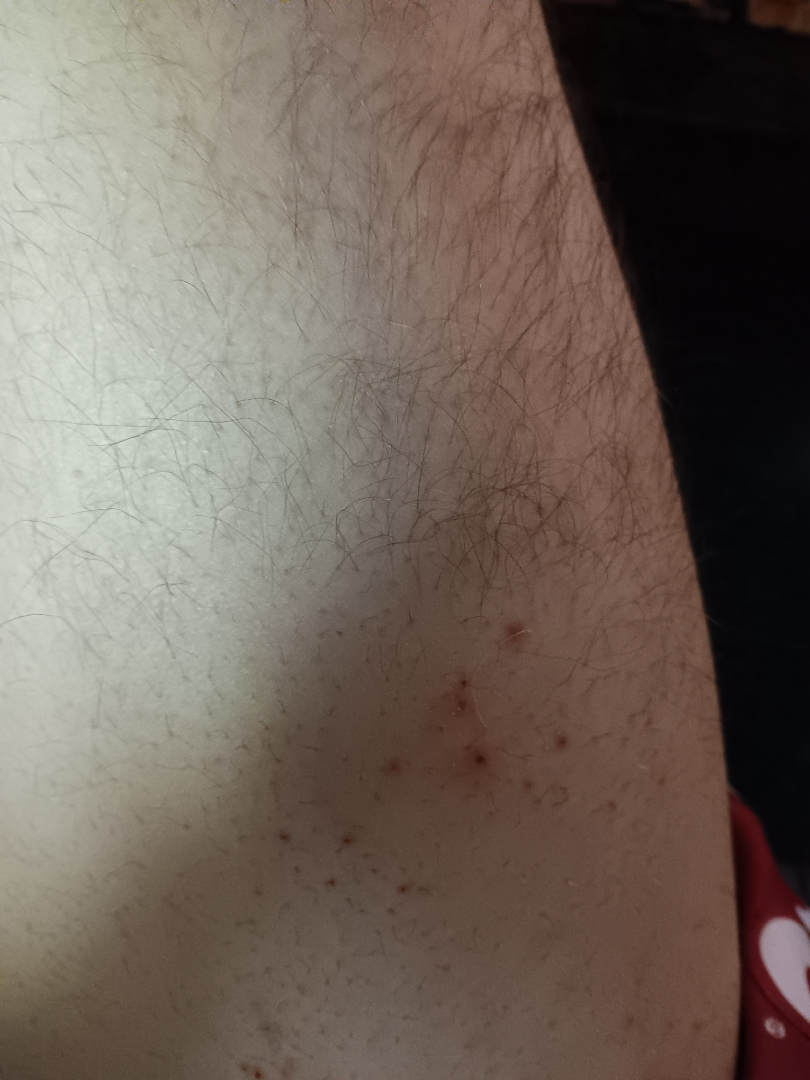assessment: indeterminate | subject: male, age 40–49 | photo taken: close-up | affected area: leg and back of the hand.